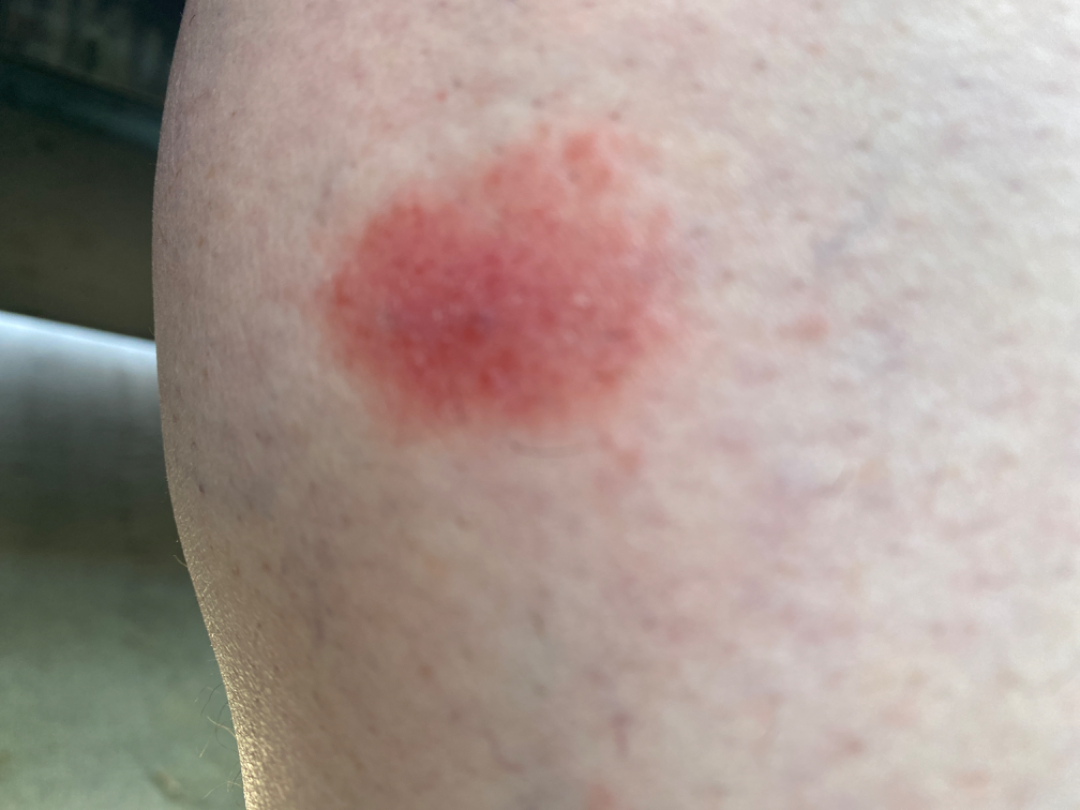The patient is a female aged 40–49. An image taken at an angle. Present for three to twelve months. The affected area is the leg. Self-categorized by the patient as a rash. Most likely Pigmented purpuric eruption; also consider Eczema; possibly Allergic Contact Dermatitis; lower on the differential is Localized cutaneous vasculitis; less likely is Necrobiosis lipoidica.